A dermoscopic close-up of a skin lesion:
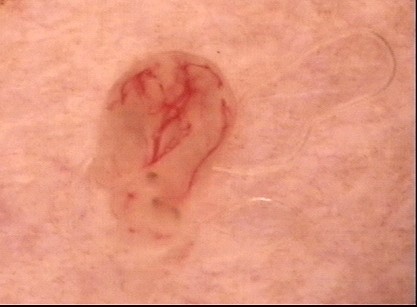Conclusion:
The diagnostic label was a dermal nevus.